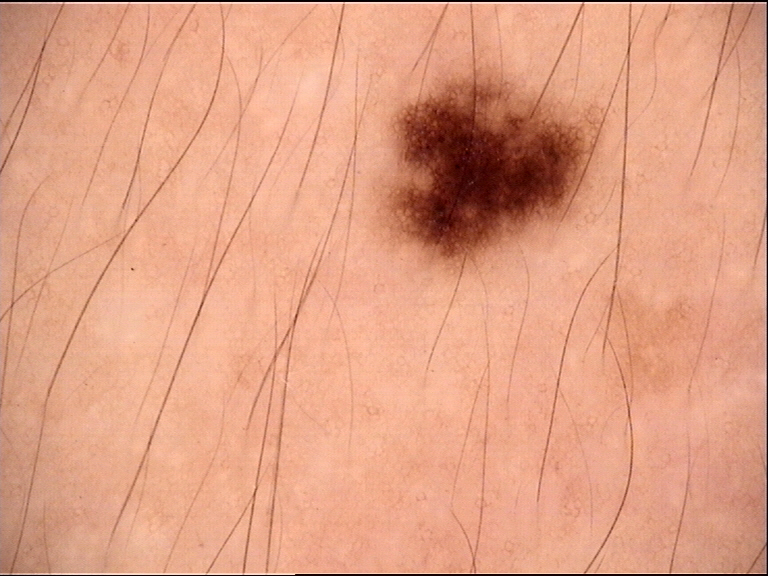Dermoscopy of a skin lesion.
Classified as a banal lesion — a junctional nevus.